A dermoscopy image of a single skin lesion:
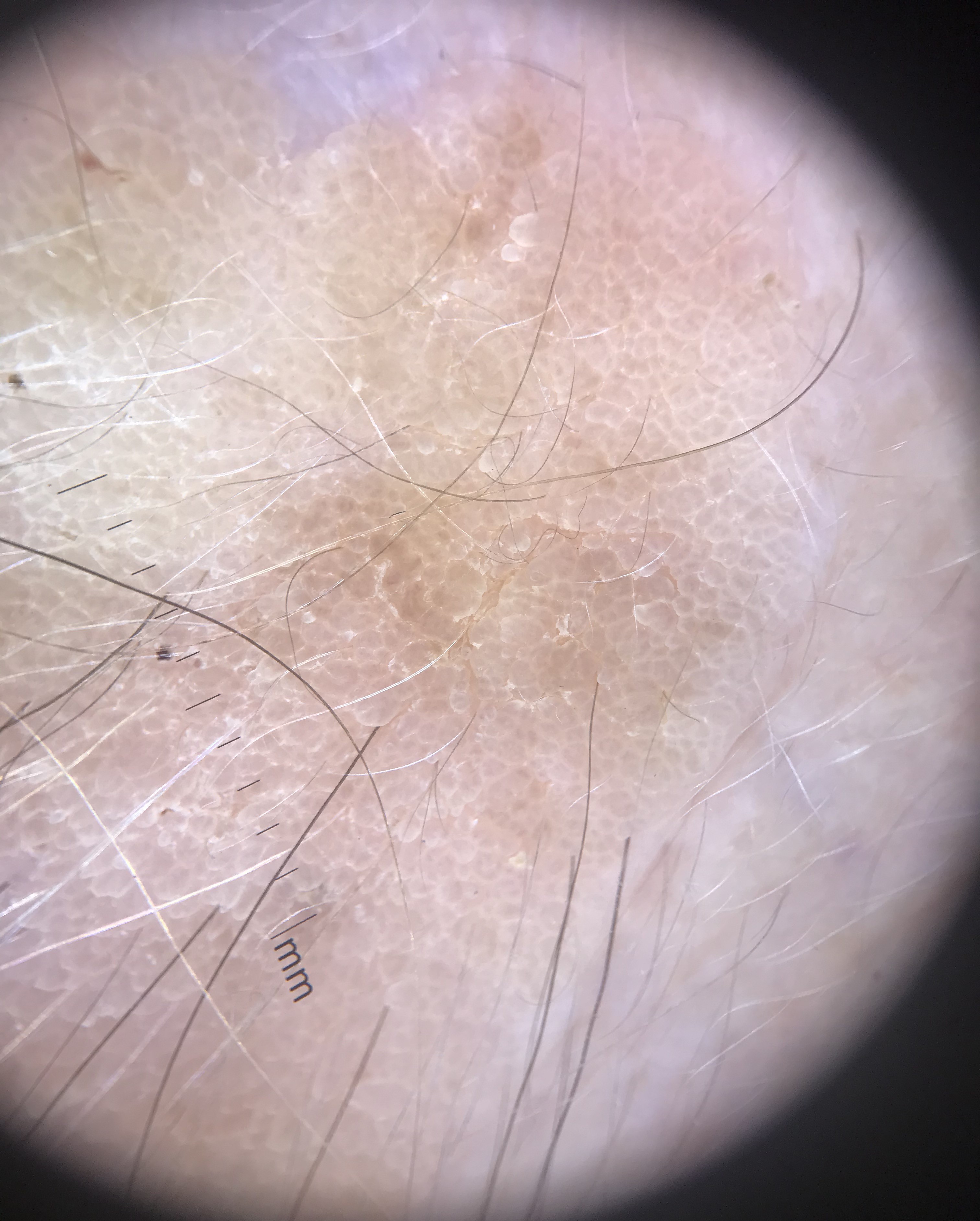The morphology is that of a keratinocytic lesion.
Classified as a benign lesion — a seborrheic keratosis.